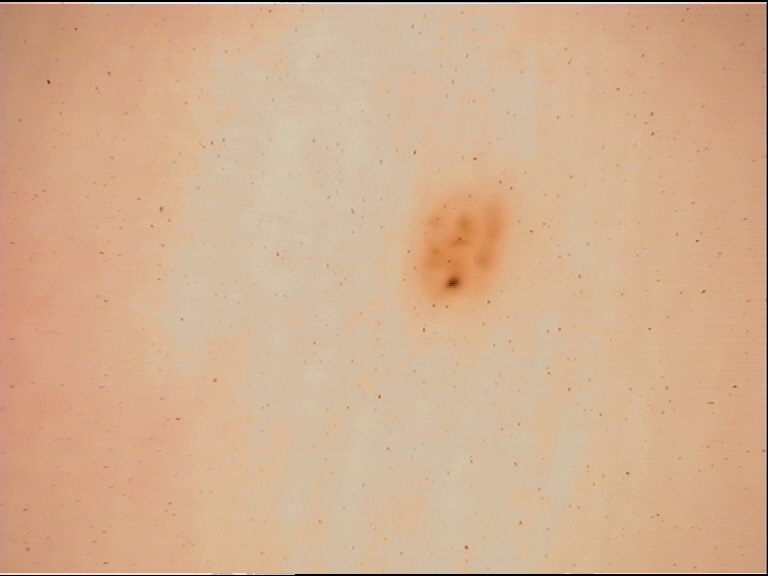Q: What was the diagnostic impression?
A: acral junctional nevus (expert consensus)